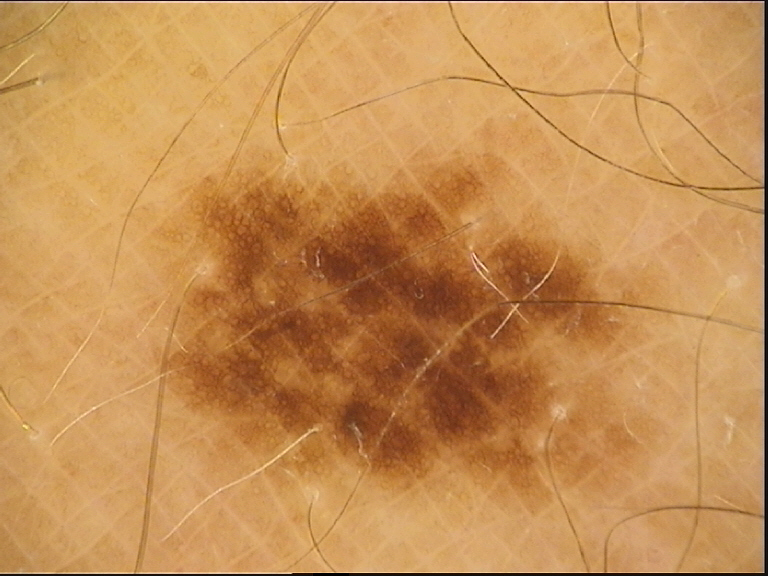Findings: A dermatoscopic image of a skin lesion. Conclusion: The diagnostic label was a dysplastic junctional nevus.